The affected area is the leg · a close-up photograph:
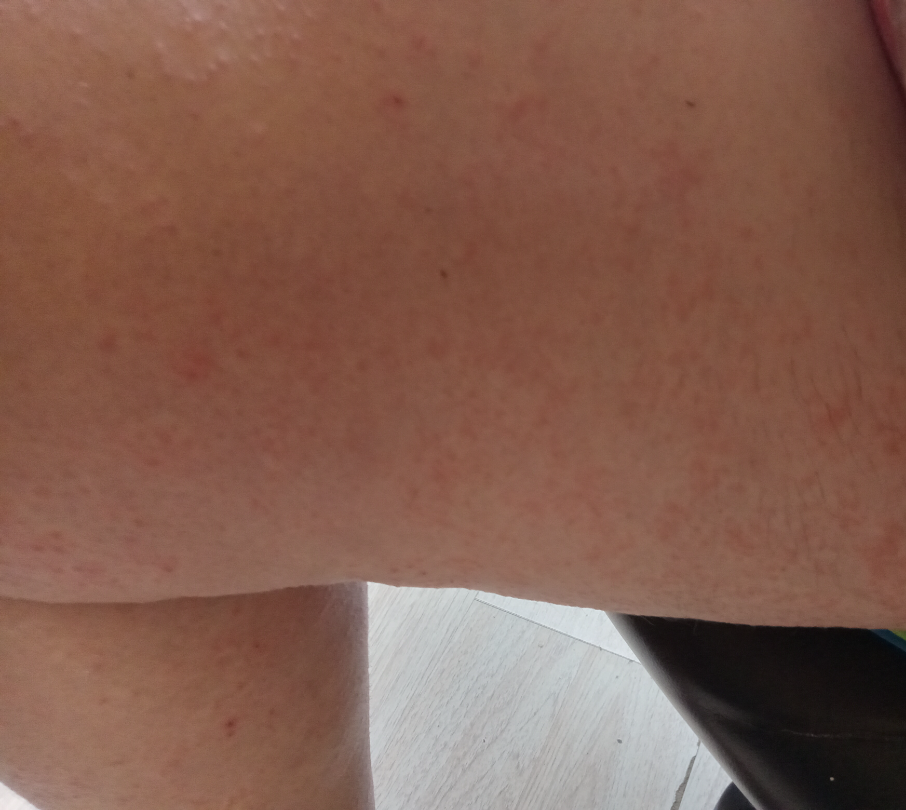No differential diagnosis could be assigned on photographic review.